A female patient aged approximately 75 · an overview clinical photograph of a skin lesion · the patient is Fitzpatrick II: 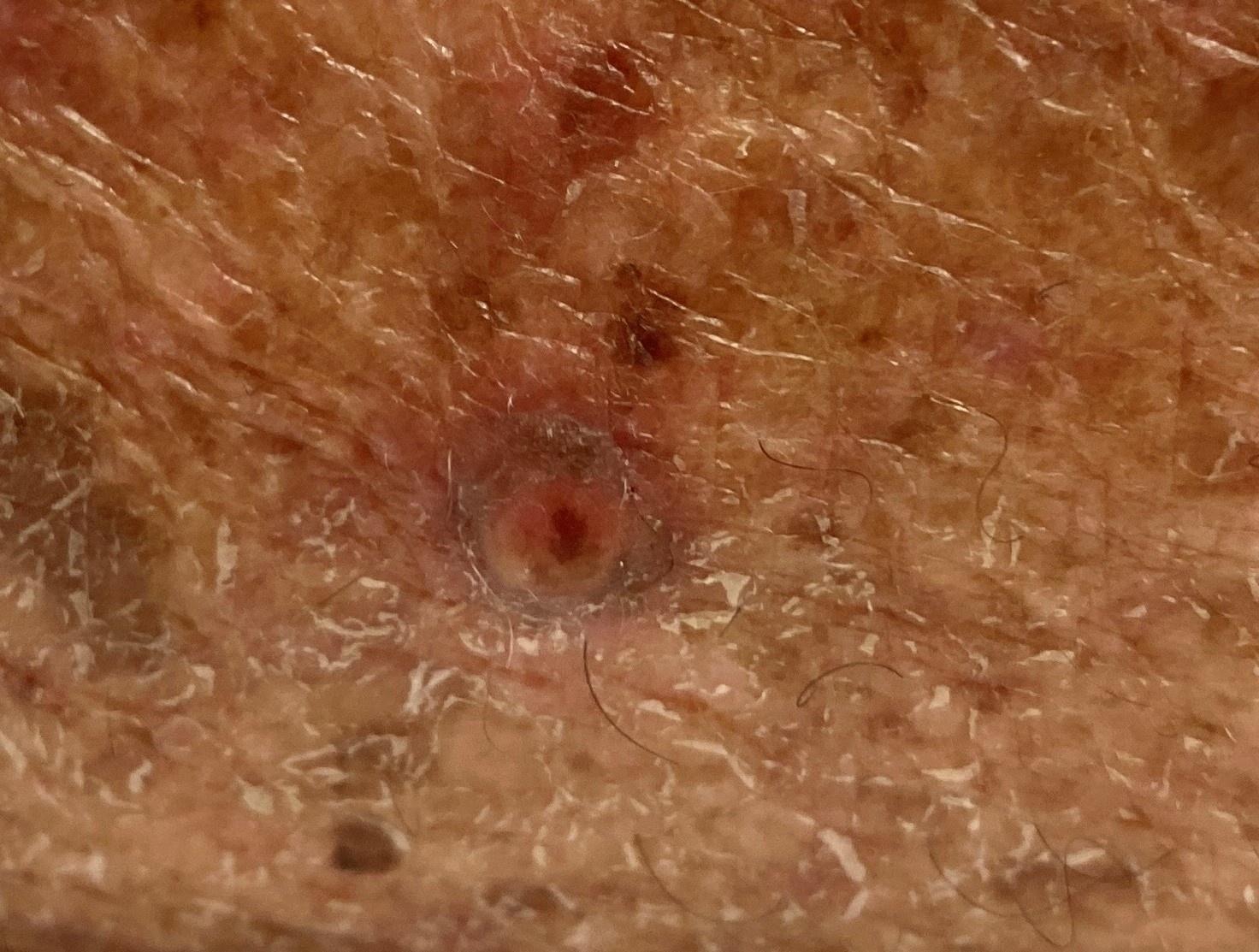The lesion is on an upper extremity.
Biopsy-confirmed as a malignancy — a squamous cell carcinoma.